A clinical overview photograph of a skin lesion. A male patient aged around 80.
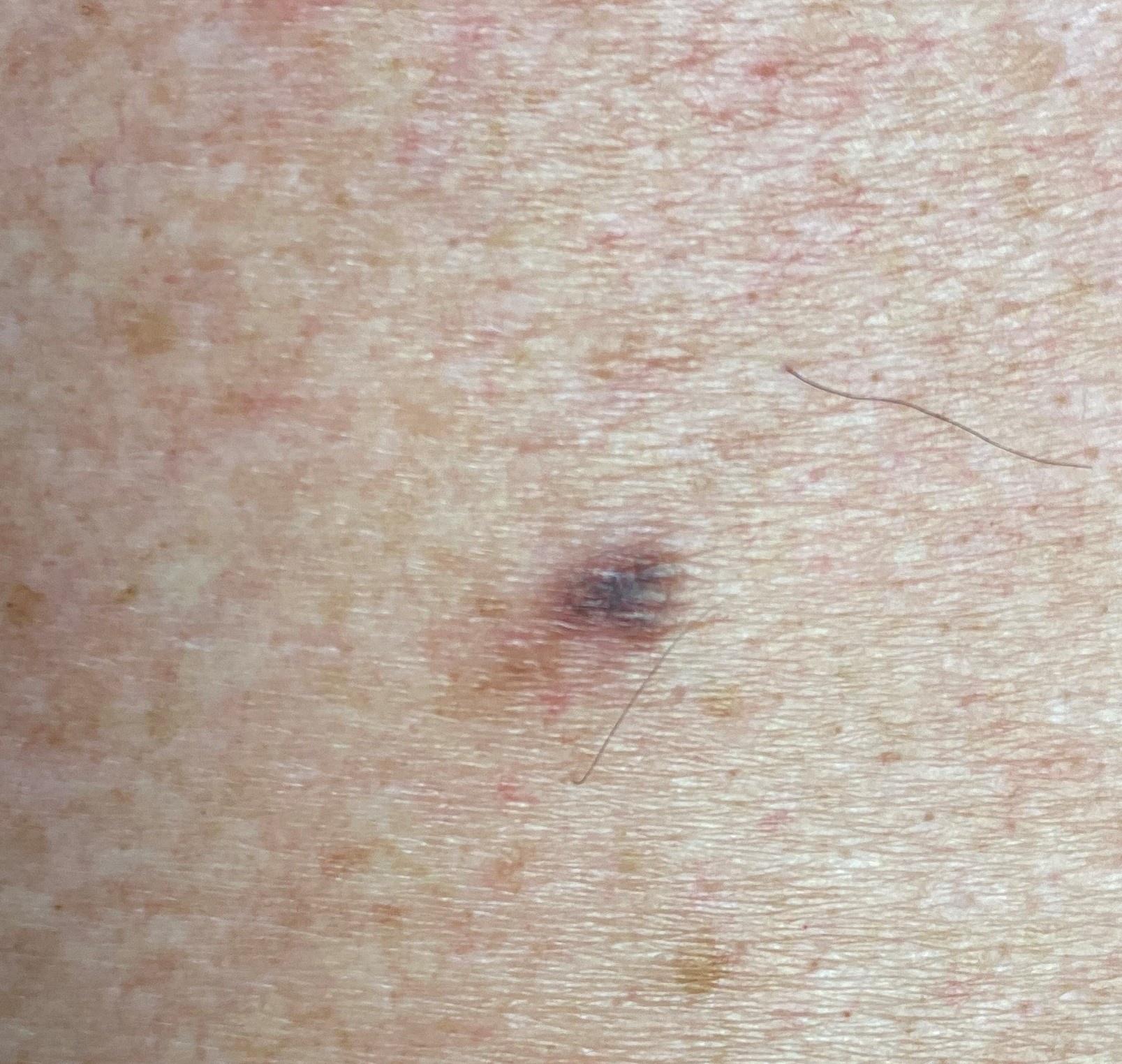site: the posterior trunk | diagnosis: Melanoma (biopsy-proven).